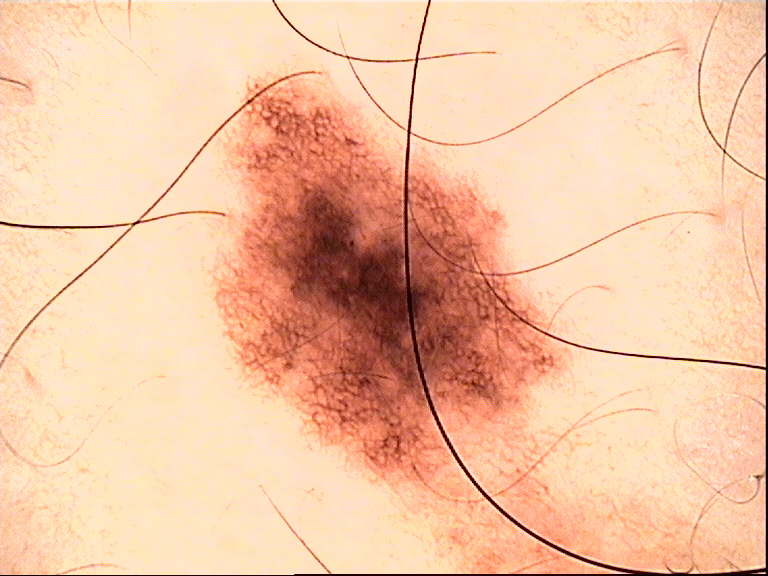Classified as a benign lesion — a dysplastic compound nevus.